A male subject, about 75 years old · a dermoscopic image of a skin lesion — 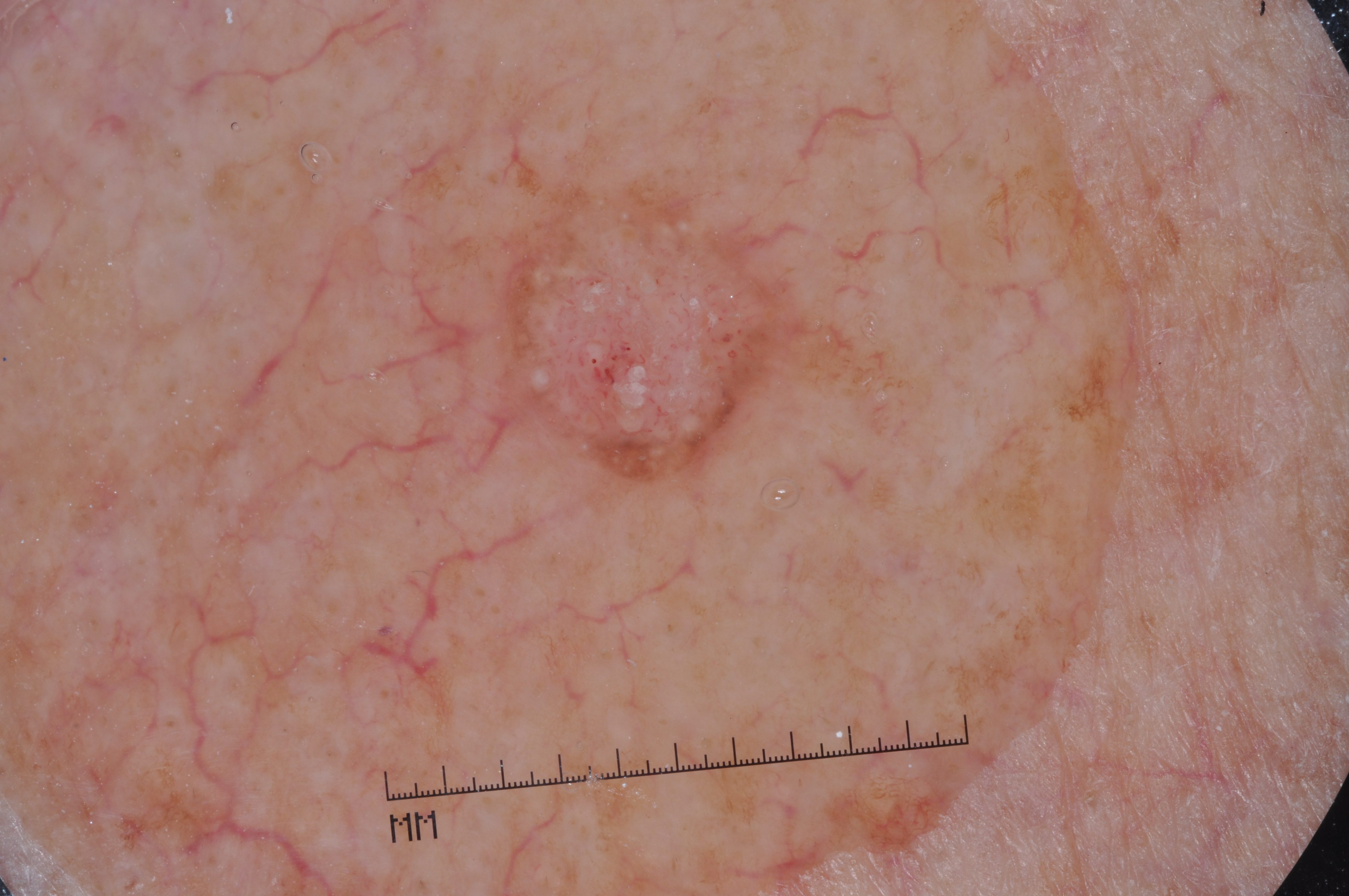Image and clinical context: In (x1, y1, x2, y2) order, lesion location: 475, 155, 819, 501. Dermoscopically, the lesion shows milia-like cysts. Impression: The lesion was assessed as a seborrheic keratosis, a benign lesion.